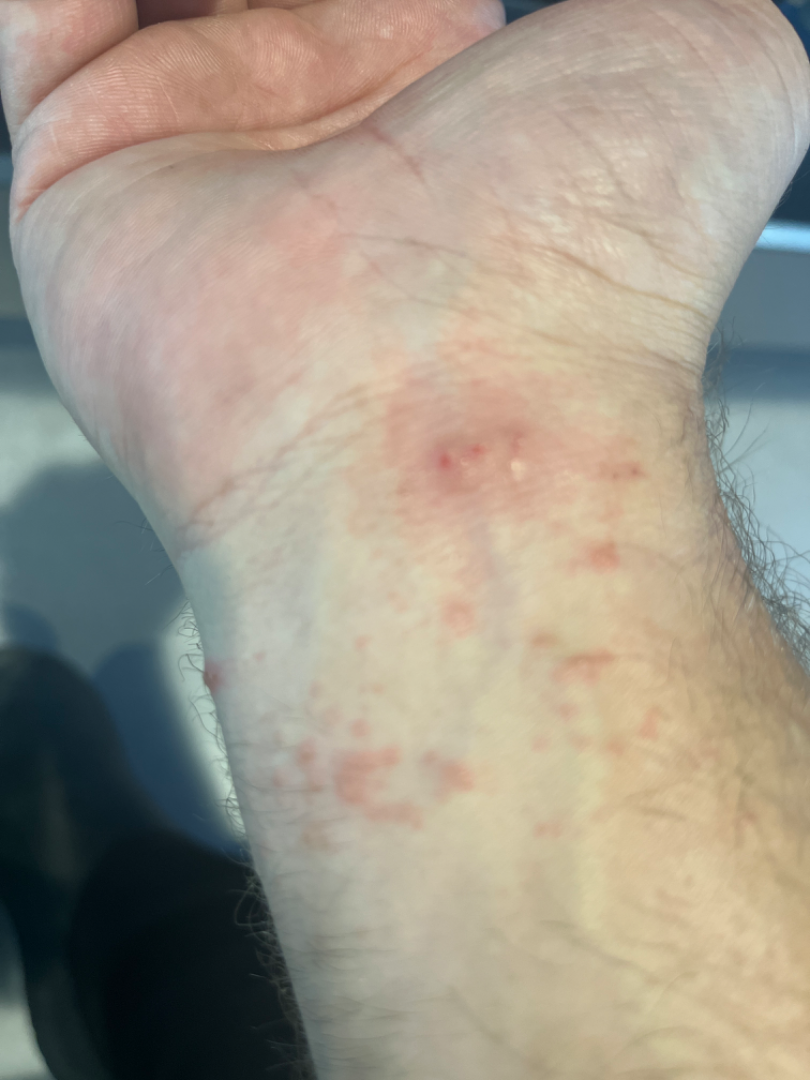A close-up photograph. On remote review of the image: Eczema (1.00).